Present for three to twelve months · the photo was captured at an angle · the affected area is the leg · texture is reported as flat: 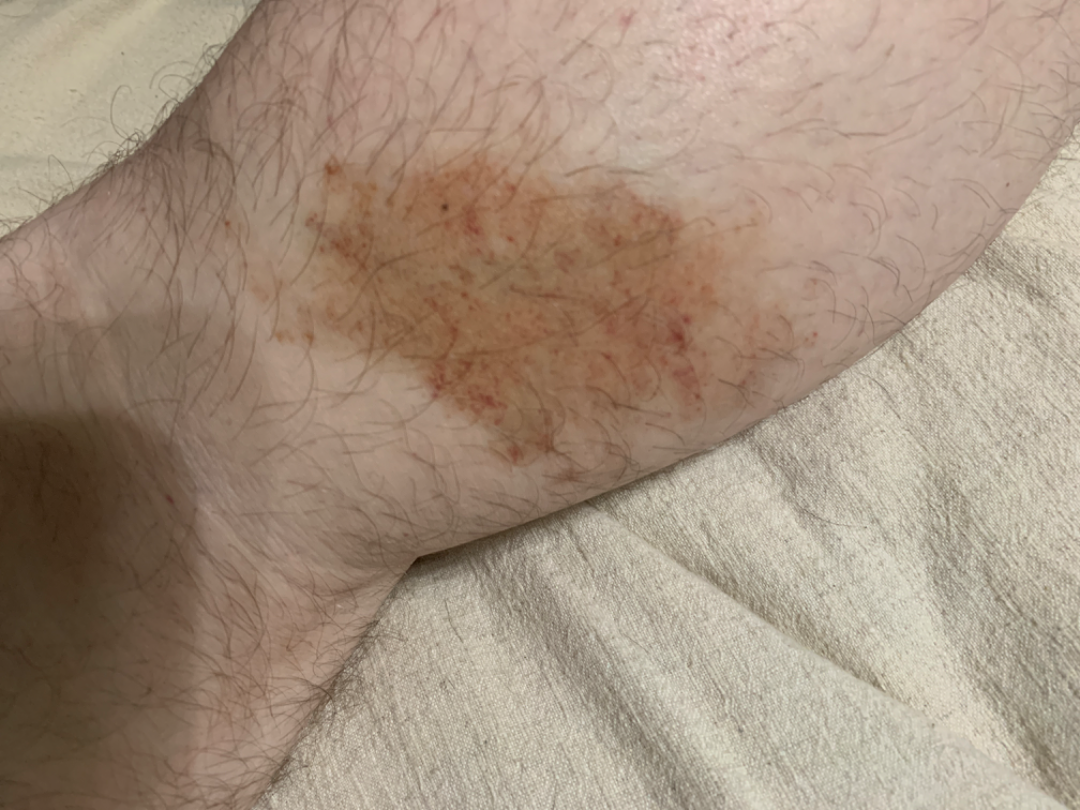{"differential": {"tied_lead": ["Pigmented purpuric eruption", "Irritant Contact Dermatitis"]}}